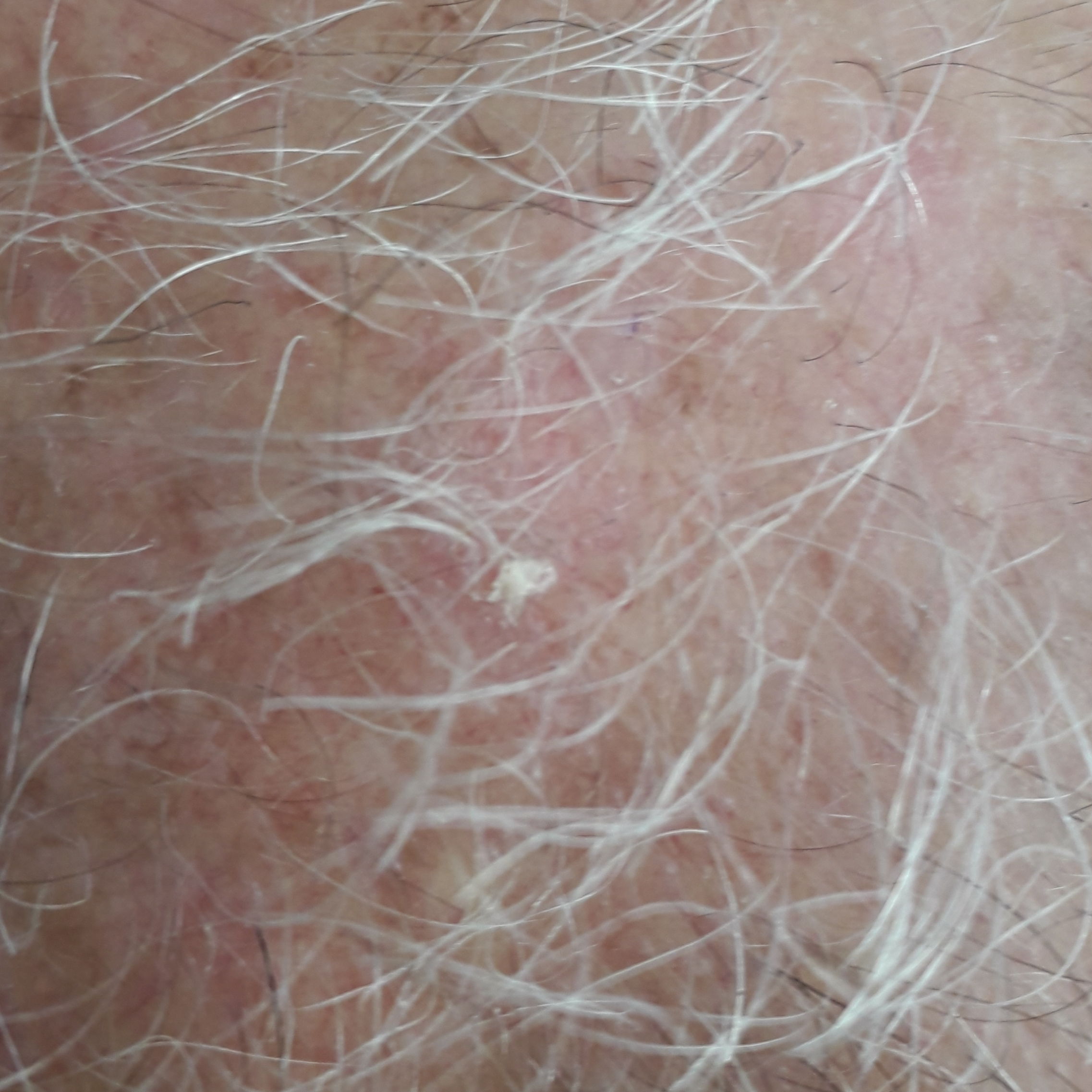Q: What are the relevant risk factors?
A: prior malignancy (patient or family), no prior skin cancer (patient or family)
Q: How was this image acquired?
A: clinical photograph
Q: What is the anatomic site?
A: the scalp
Q: How large is the lesion?
A: 8 × 8 mm
Q: What does the patient describe?
A: none reported
Q: What was the clinical impression?
A: actinic keratosis (clinical consensus)